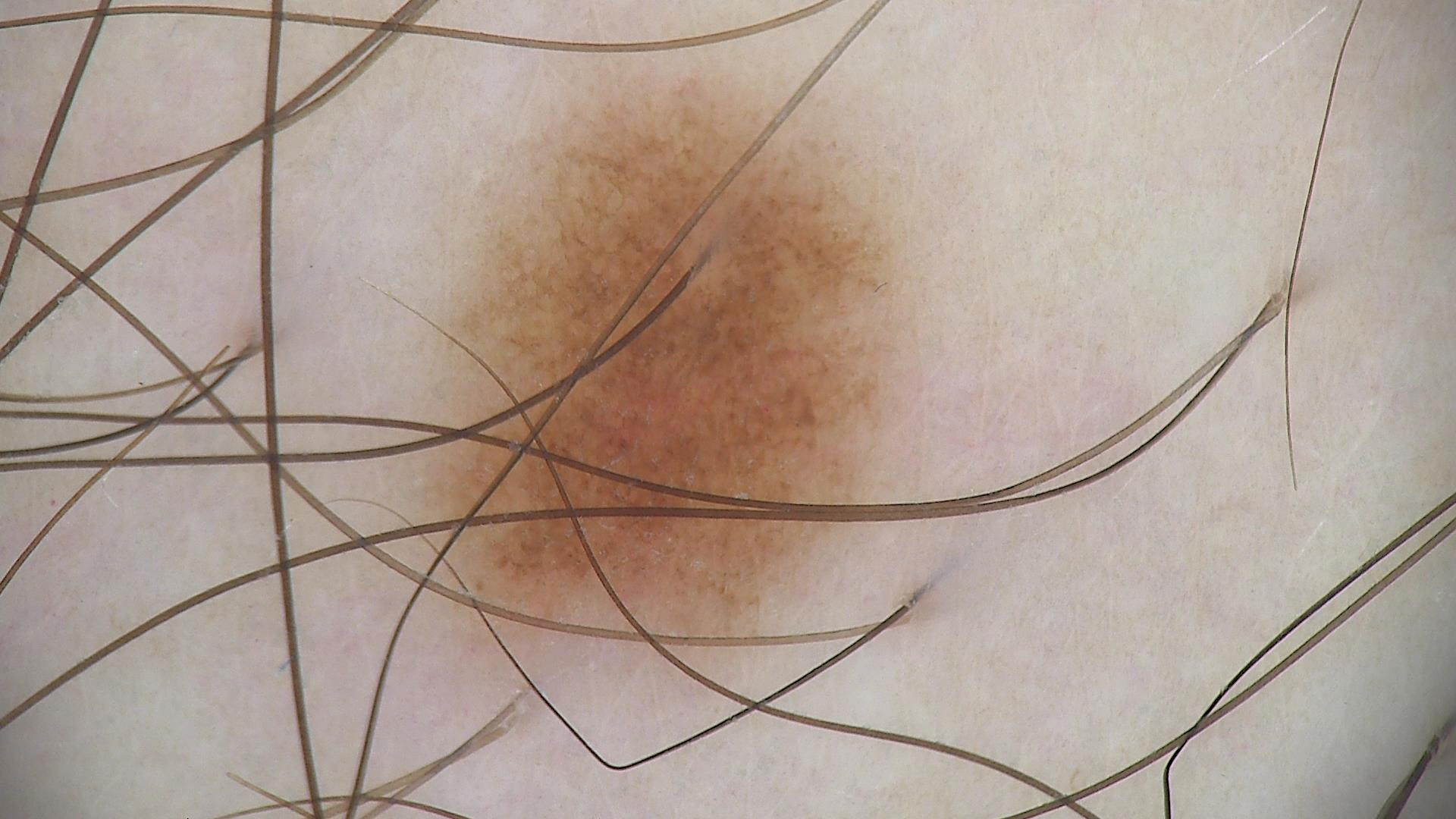A dermoscopic image of a skin lesion.
Classified as a dysplastic junctional nevus.